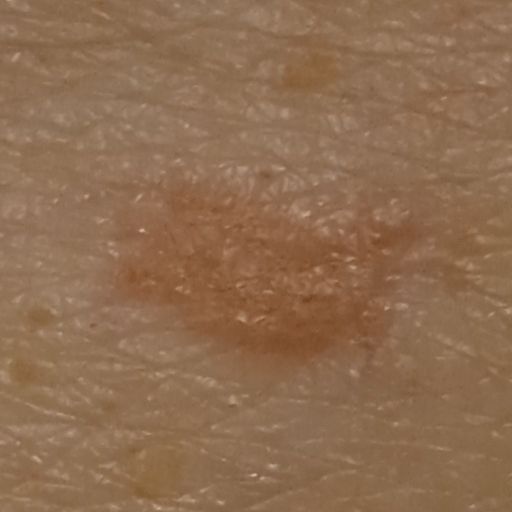{"referral": "clinical suspicion of basal cell carcinoma", "sun_reaction": "skin tans without first burning", "risk_factors": {"positive": ["a personal history of cancer"], "negative": ["no sunbed use"]}, "image": "clinical photograph", "patient": {"age": 84, "sex": "female"}, "lesion_location": "the torso", "lesion_size": {"diameter_mm": 12.5}, "diagnosis": {"name": "basal cell carcinoma", "malignancy": "malignant", "procedure": "punch biopsy", "tumor_thickness_mm": 2.0}}